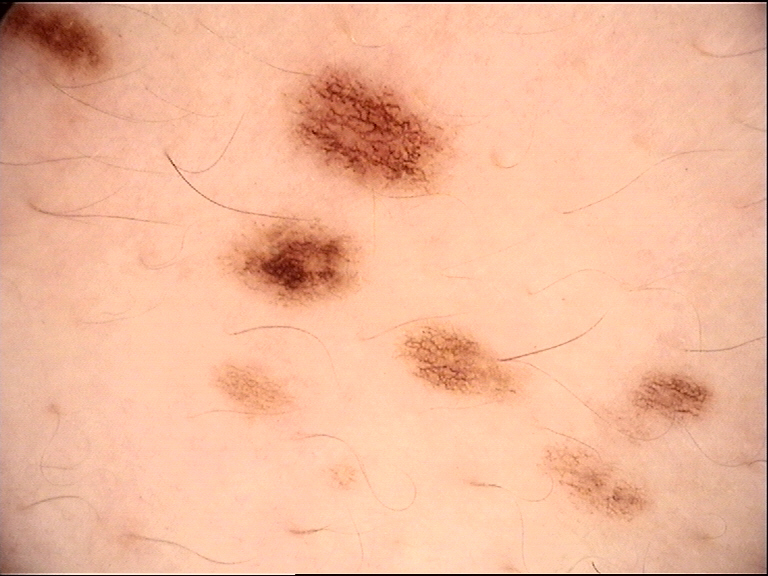A dermoscopic image of a skin lesion. Consistent with a banal lesion — a junctional nevus.